The leg is involved · the photograph was taken at an angle.
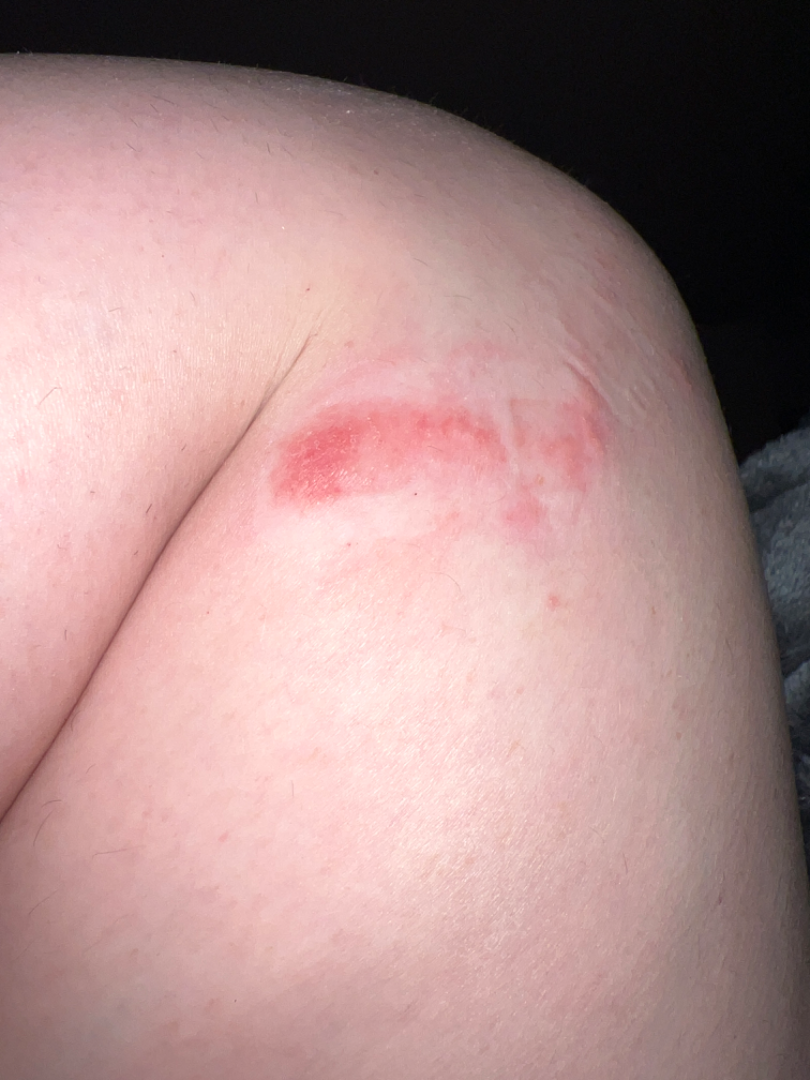differential: Allergic Contact Dermatitis (100%).